The photo was captured at an angle. Reported duration is less than one week. The patient is male. No constitutional symptoms were reported. The lesion involves the front of the torso:
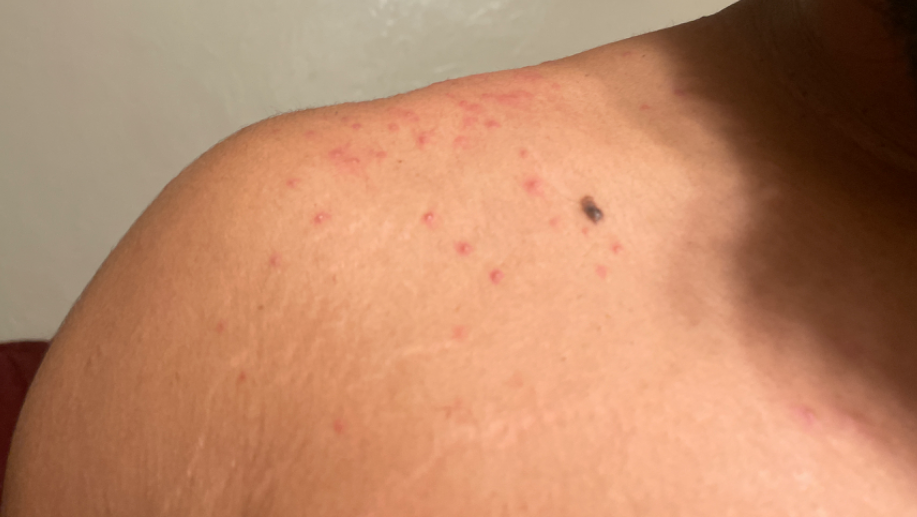Findings: The case was difficult to assess from the available photograph.